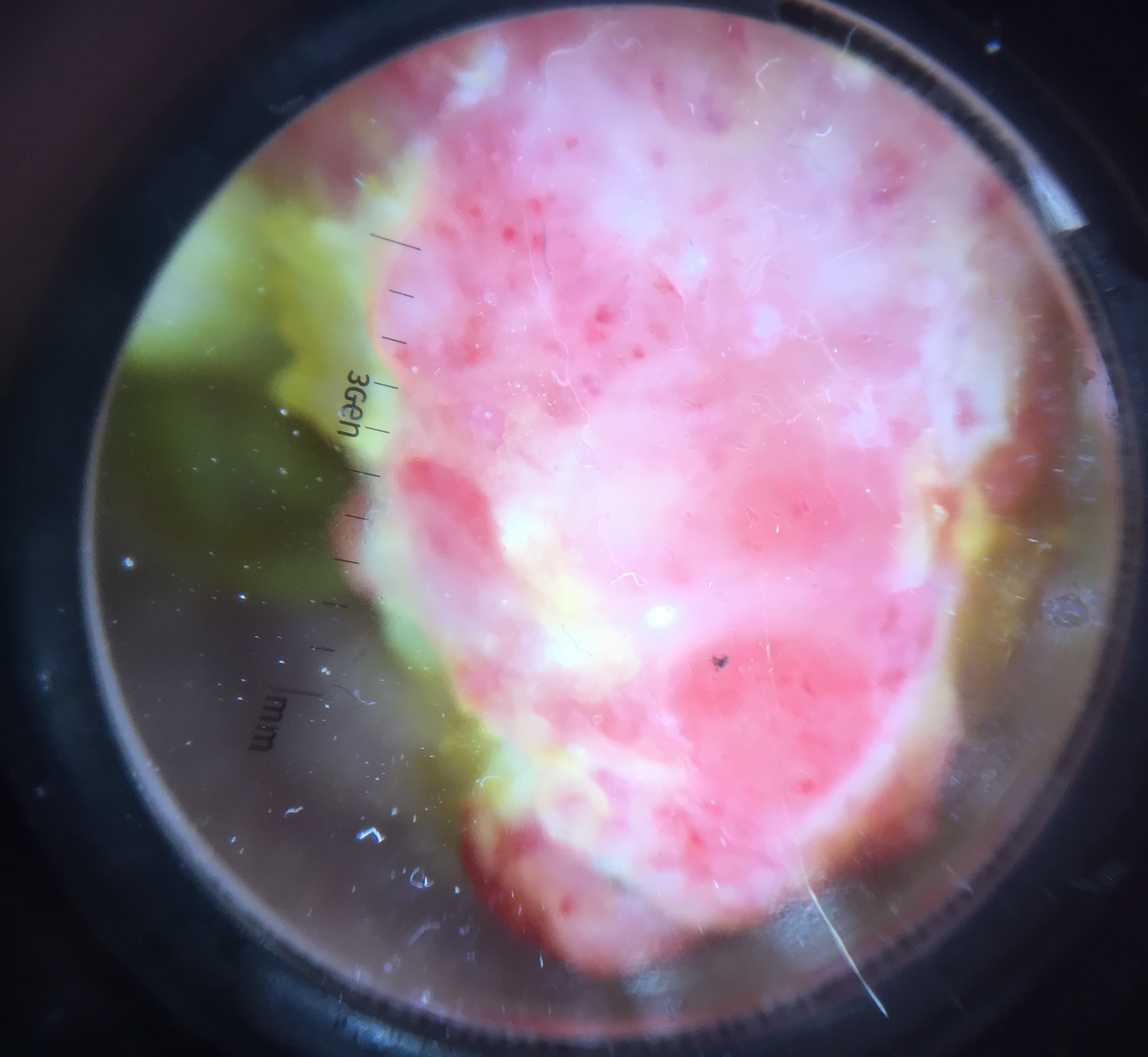Findings:
- label · acral nodular melanoma (biopsy-proven)